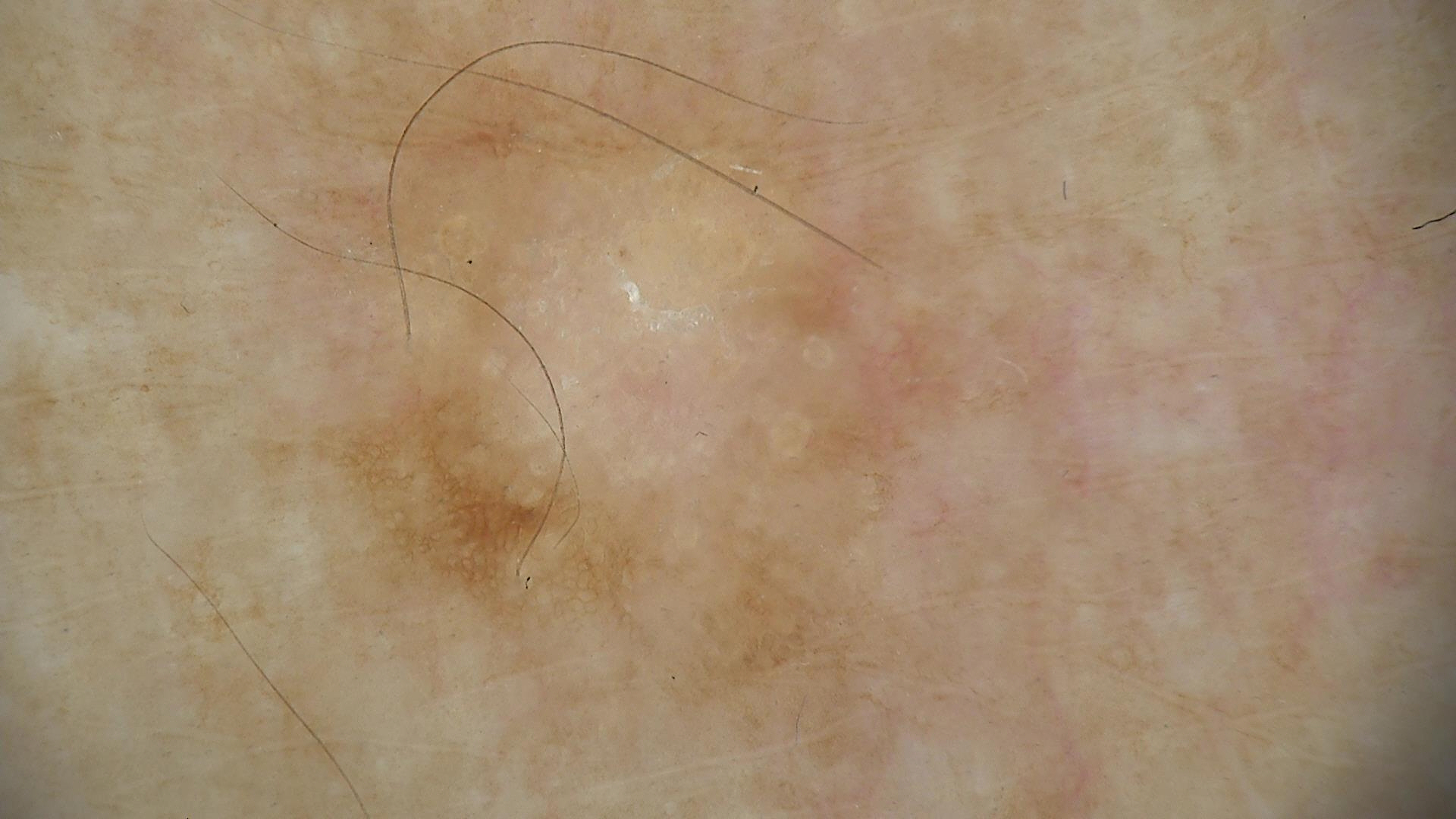label — seborrheic keratosis (expert consensus)